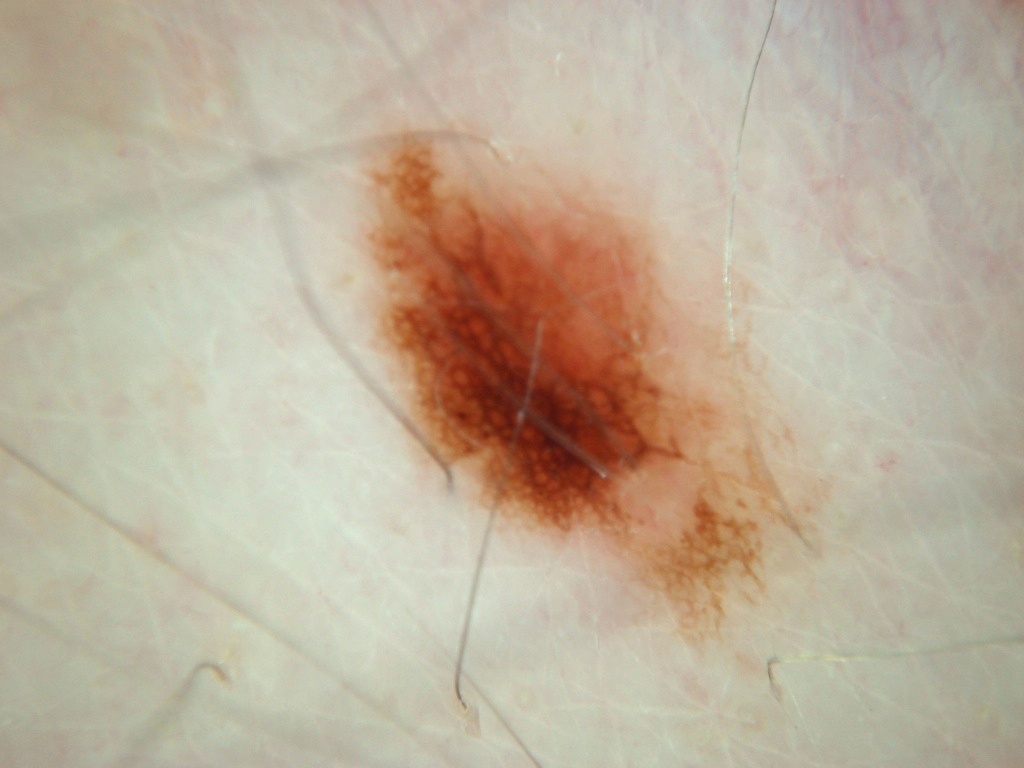This is a dermoscopic photograph of a skin lesion. On dermoscopy, the lesion shows pigment network. The lesion occupies roughly 22% of the field. In (x1, y1, x2, y2) order, the lesion spans bbox=[350, 115, 844, 662]. Biopsy-confirmed as a melanoma, a malignant skin lesion.